Located on the arm. Present for one to three months. The lesion is associated with bothersome appearance. Texture is reported as flat. The photo was captured at an angle. Self-categorized by the patient as a pigmentary problem. No constitutional symptoms were reported.
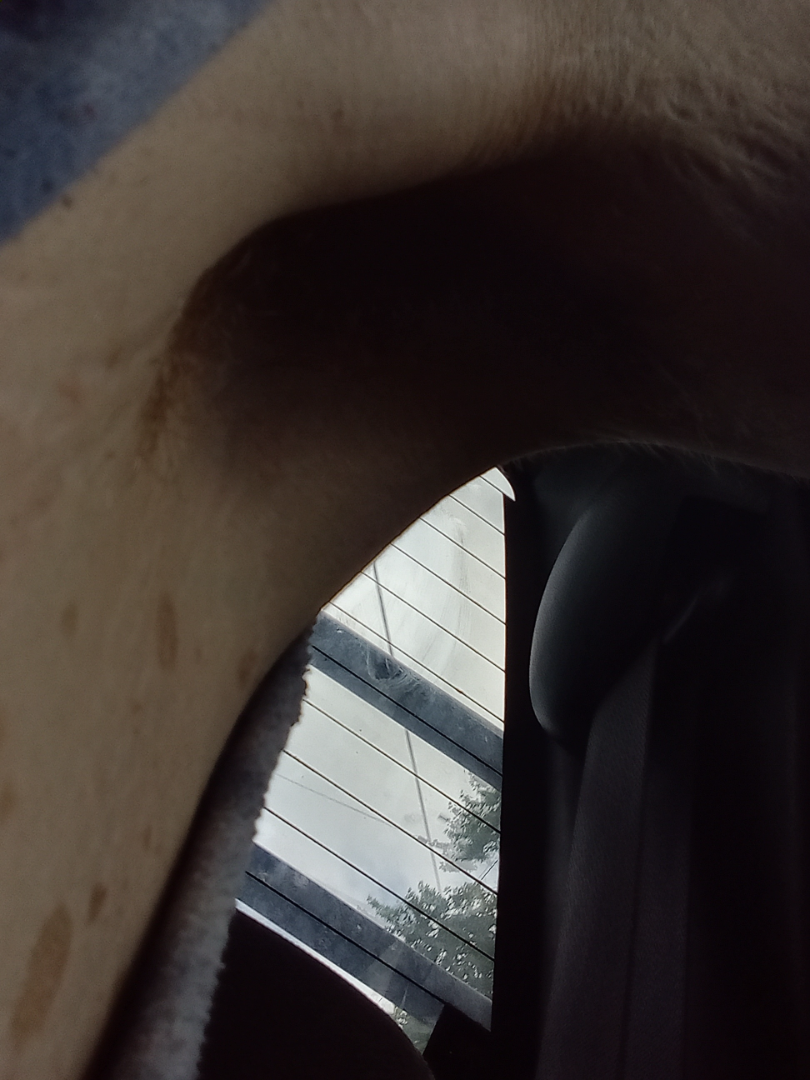No differential diagnosis could be assigned on photographic review.